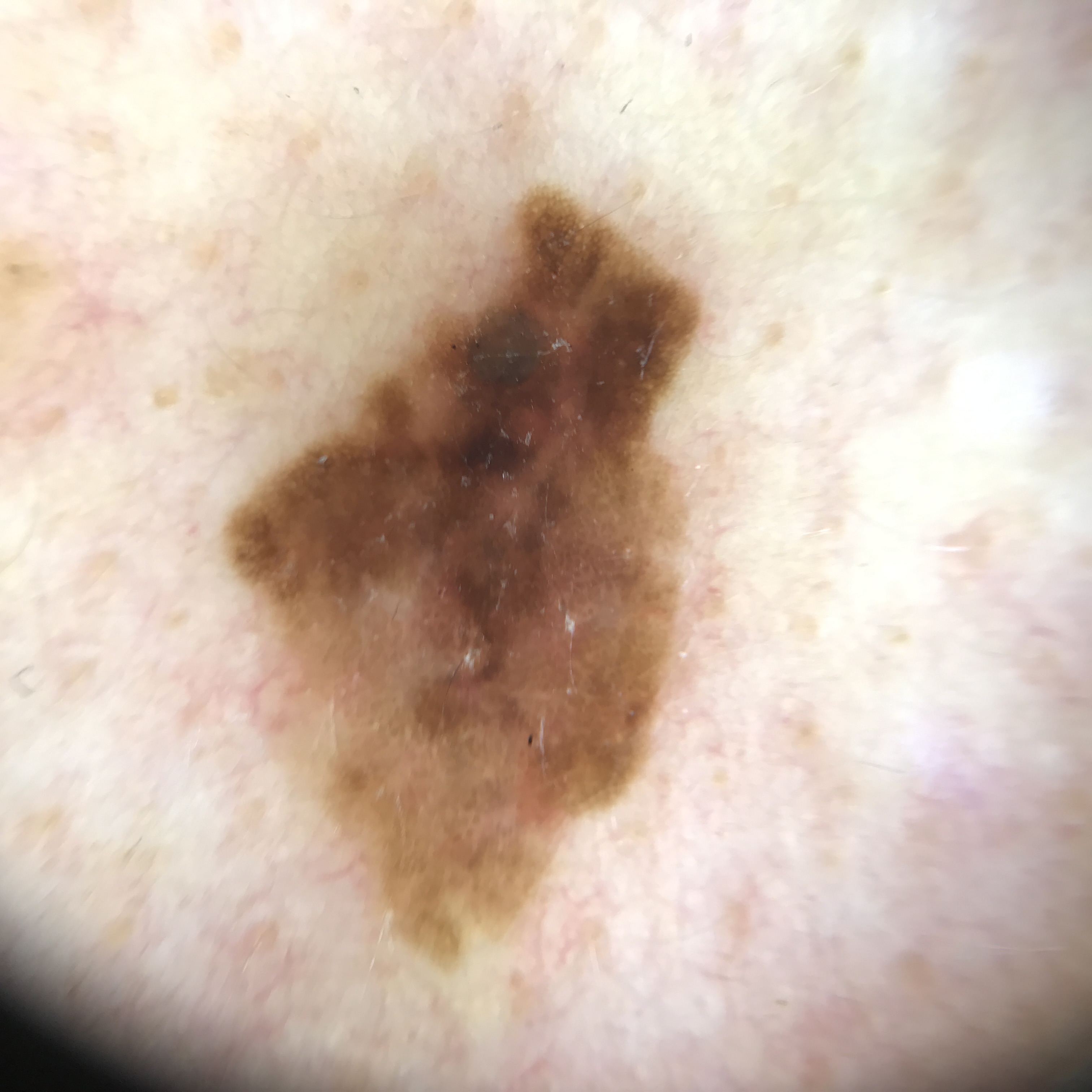image type: dermoscopy
label: melanoma (biopsy-proven)